A skin lesion imaged with a dermatoscope:
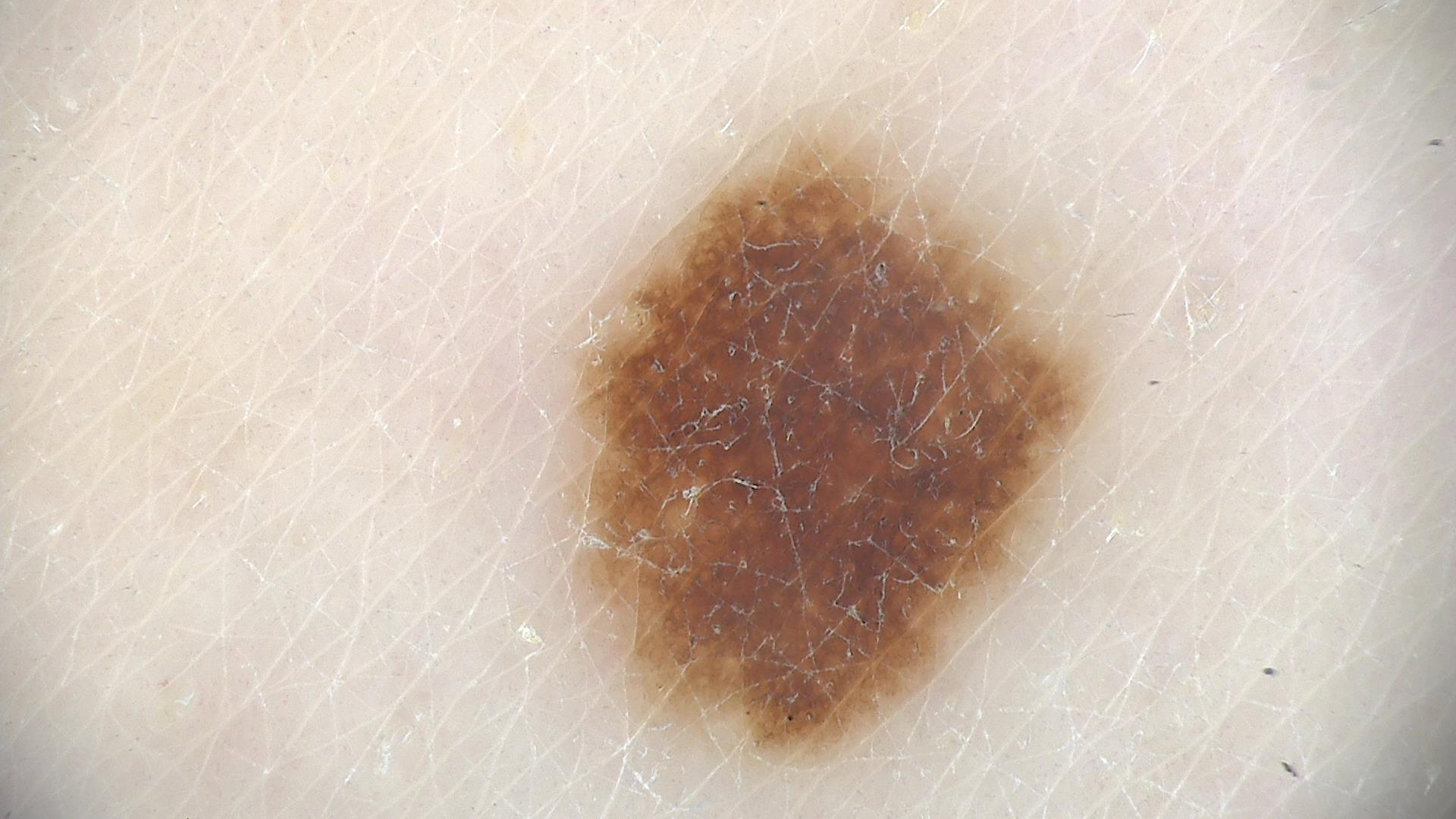Summary: The morphology is that of a banal lesion. Conclusion: Labeled as a congenital junctional nevus.